This image was taken at an angle; the head or neck and arm are involved: 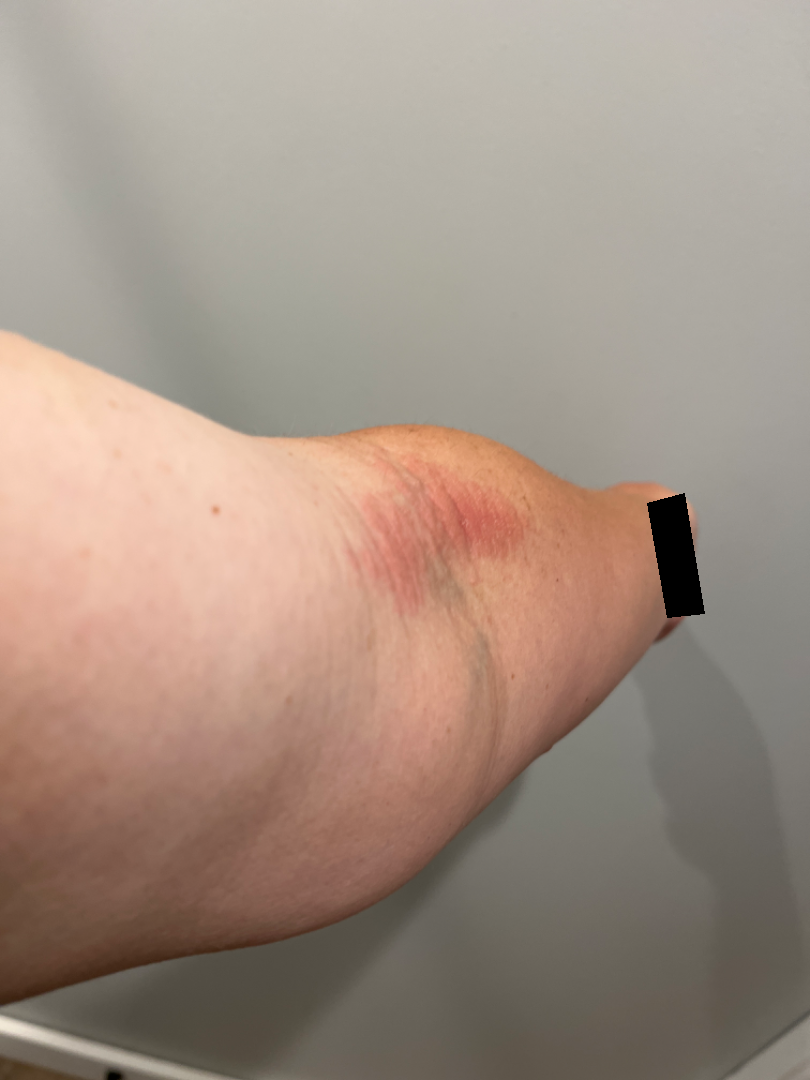Clinical context: The lesion is associated with itching. Self-categorized by the patient as a rash. The condition has been present for less than one week. Texture is reported as raised or bumpy. Assessment: On remote review of the image: in keeping with Eczema.